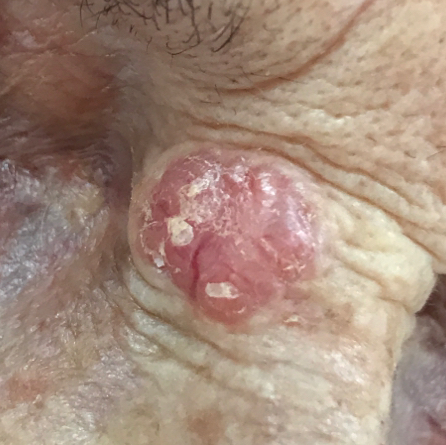Case summary: A clinical photo of a skin lesion taken with a smartphone. A female patient age 77. Located on the nose. By the patient's account, the lesion has grown, itches, and is elevated. Diagnosis: Histopathologically confirmed as a basal cell carcinoma.